The photograph was taken at a distance. The patient is female. The leg is involved: 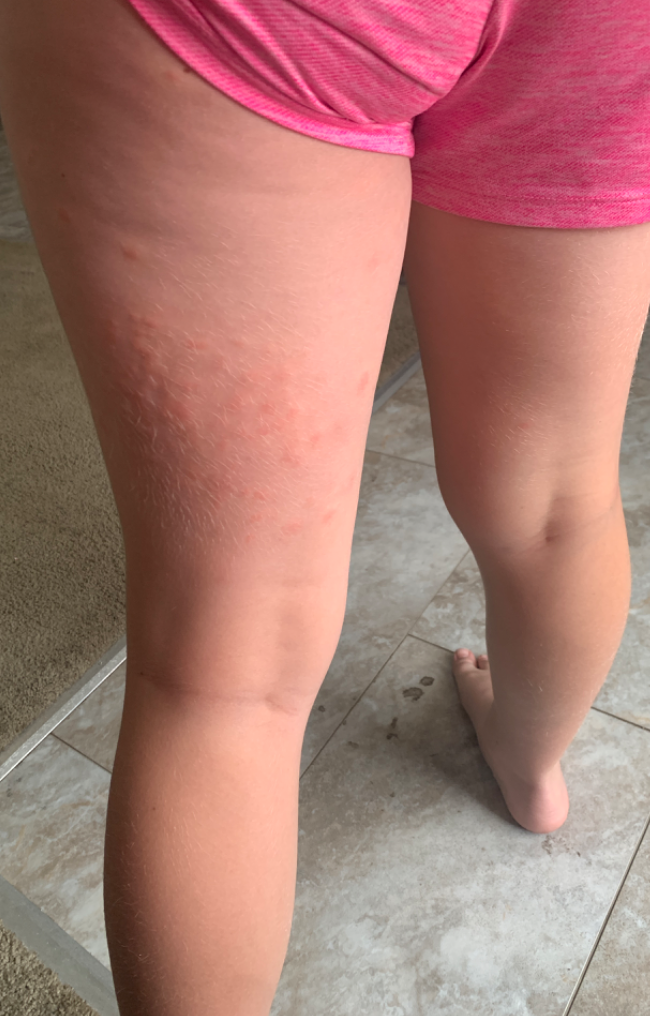<report>
<texture>raised or bumpy</texture>
<symptoms>itching</symptoms>
<differential>
  <Insect Bite>0.5</Insect Bite>
  <Urticaria>0.35</Urticaria>
  <Allergic Contact Dermatitis>0.15</Allergic Contact Dermatitis>
</differential>
</report>